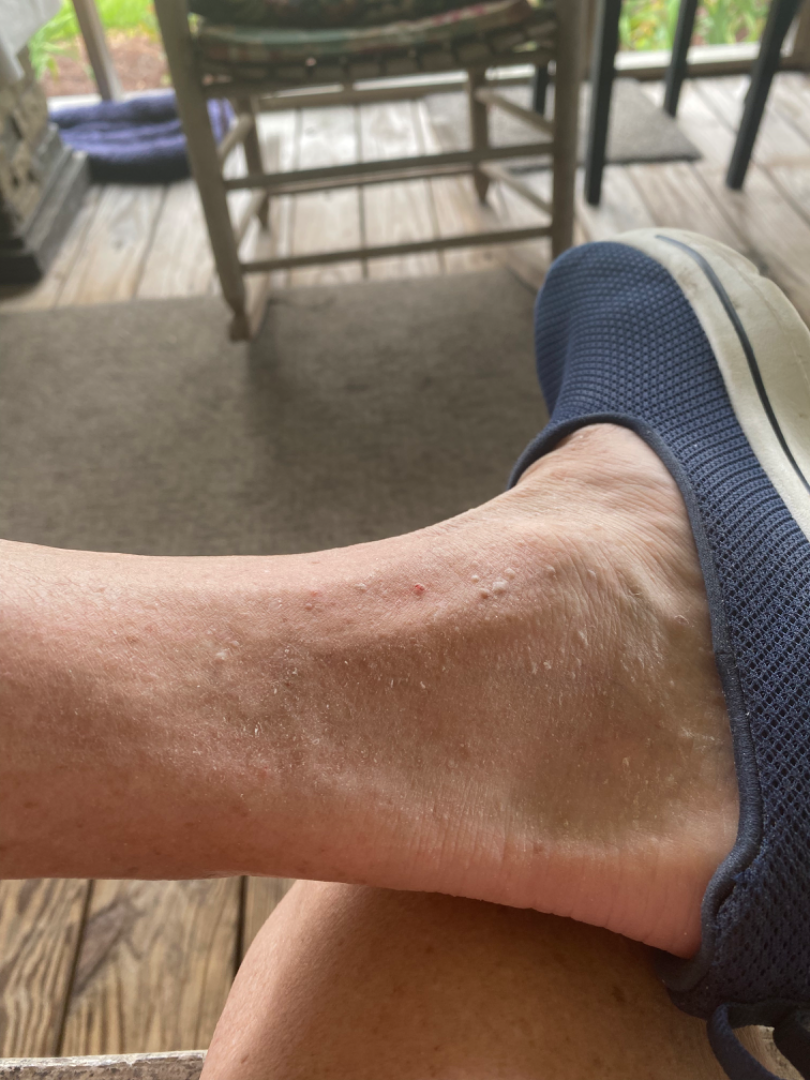{
  "body_site": "leg",
  "texture": "raised or bumpy",
  "shot_type": "at a distance"
}